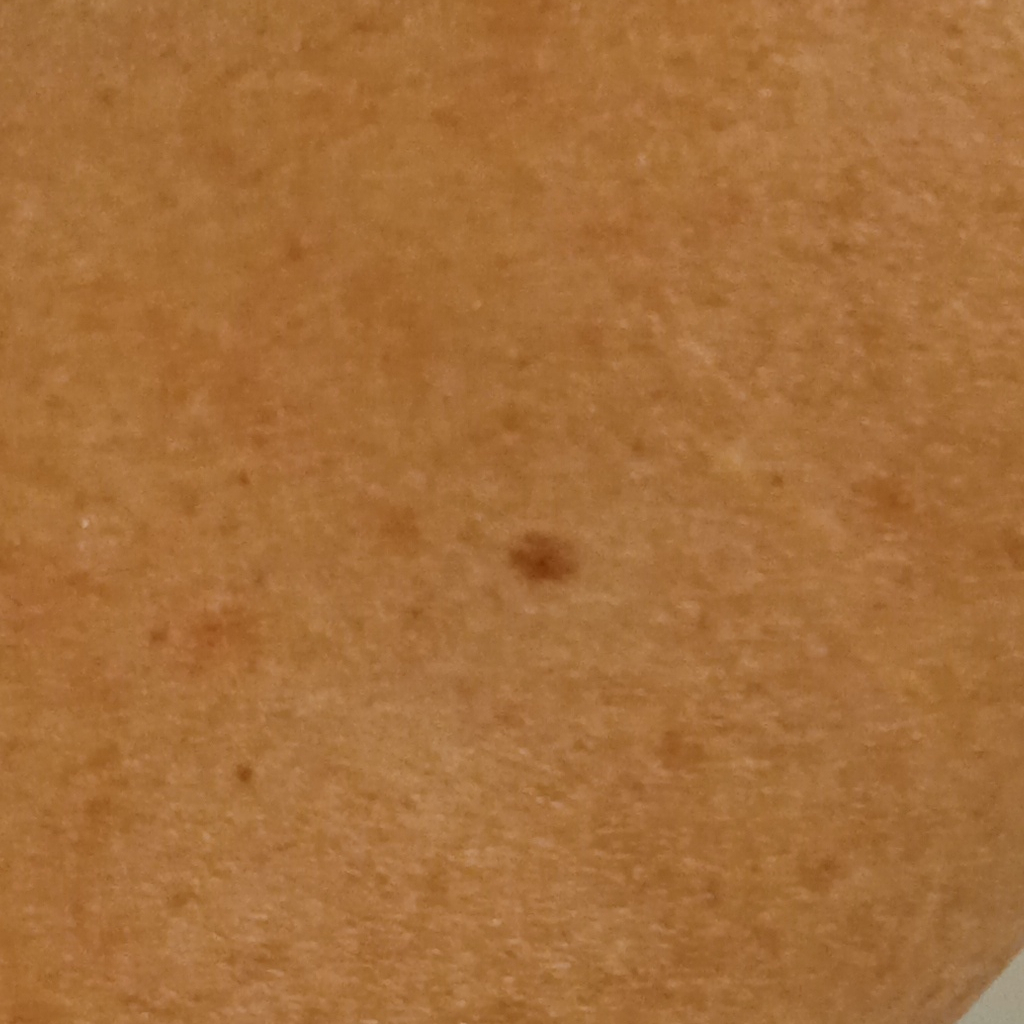Q: Patient demographics?
A: male, 72 years old
Q: What is the referral context?
A: research study (no referral diagnosis)
Q: What is the patient's nevus burden?
A: a moderate number of melanocytic nevi
Q: How does the patient's skin react to sun?
A: skin tans without first burning
Q: Where is the lesion?
A: the back
Q: How large is the lesion?
A: 3.7 mm
Q: What was the diagnosis?
A: melanocytic nevus (dermatologist consensus)